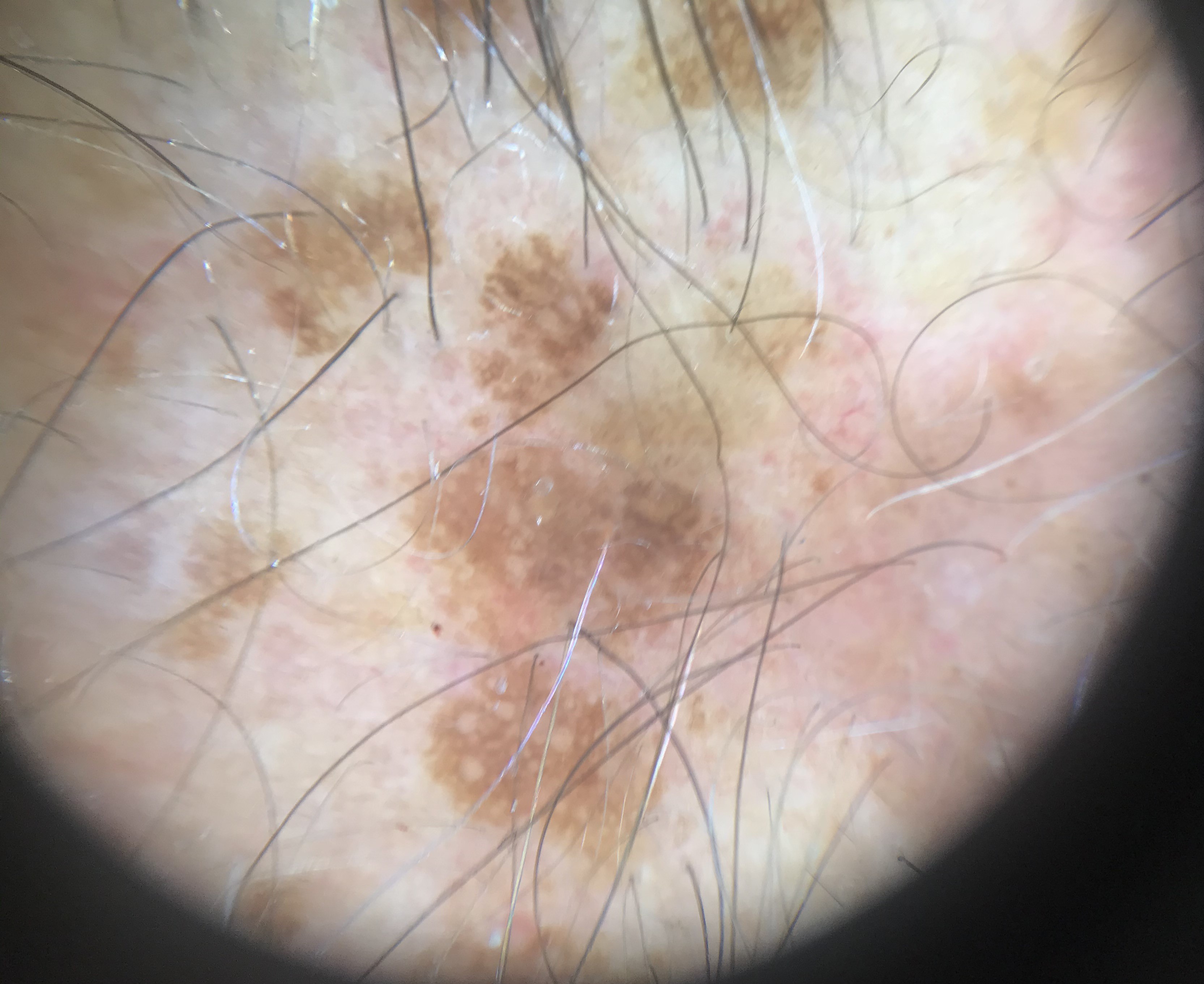Diagnosed as a seborrheic keratosis.